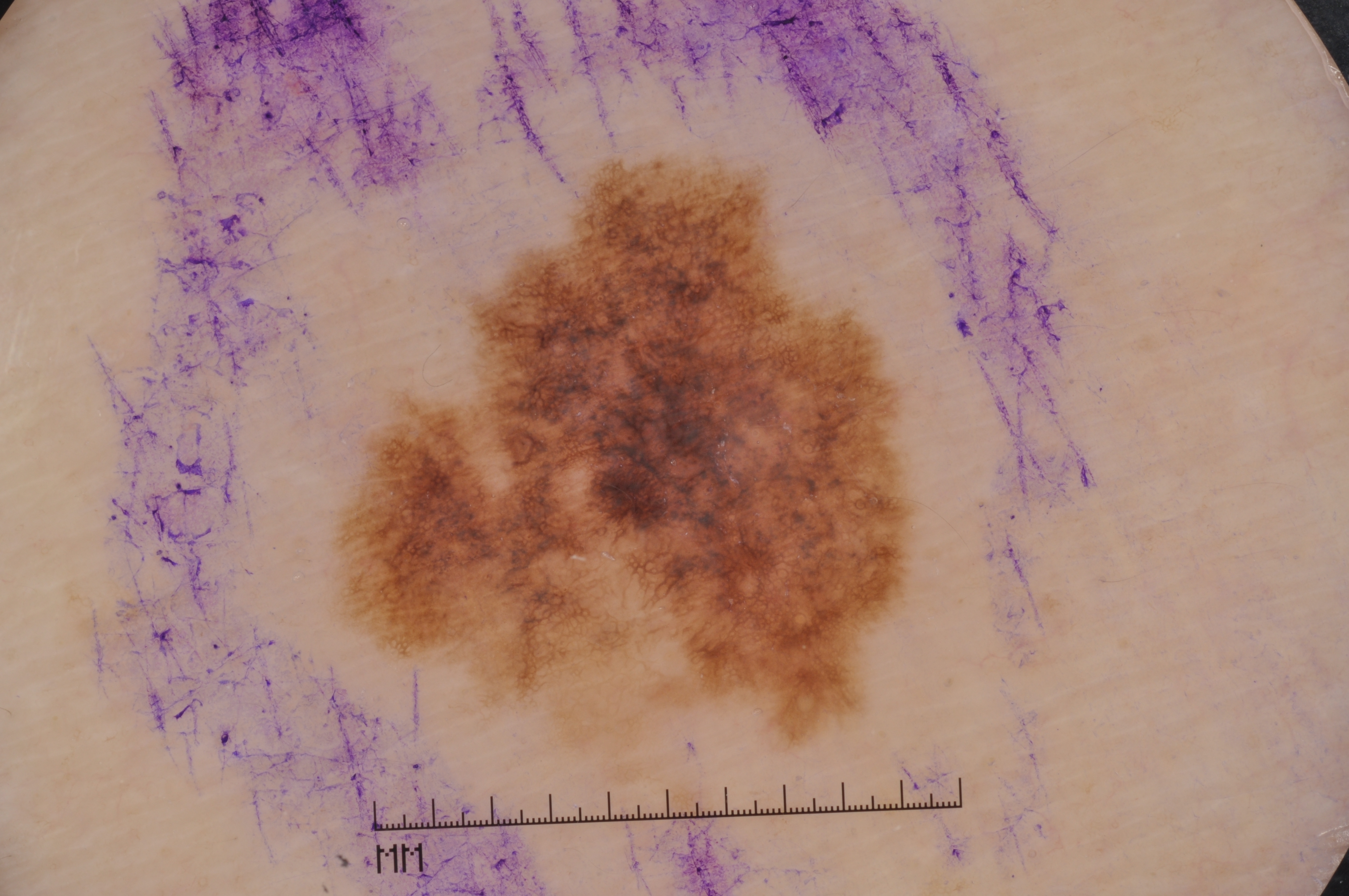Image and clinical context: The patient is a male aged around 80. A skin lesion imaged with a dermatoscope. On dermoscopy, the lesion shows milia-like cysts and pigment network. Lesion location: <bbox>318, 142, 935, 792</bbox>. Conclusion: Histopathologically confirmed as a melanoma.